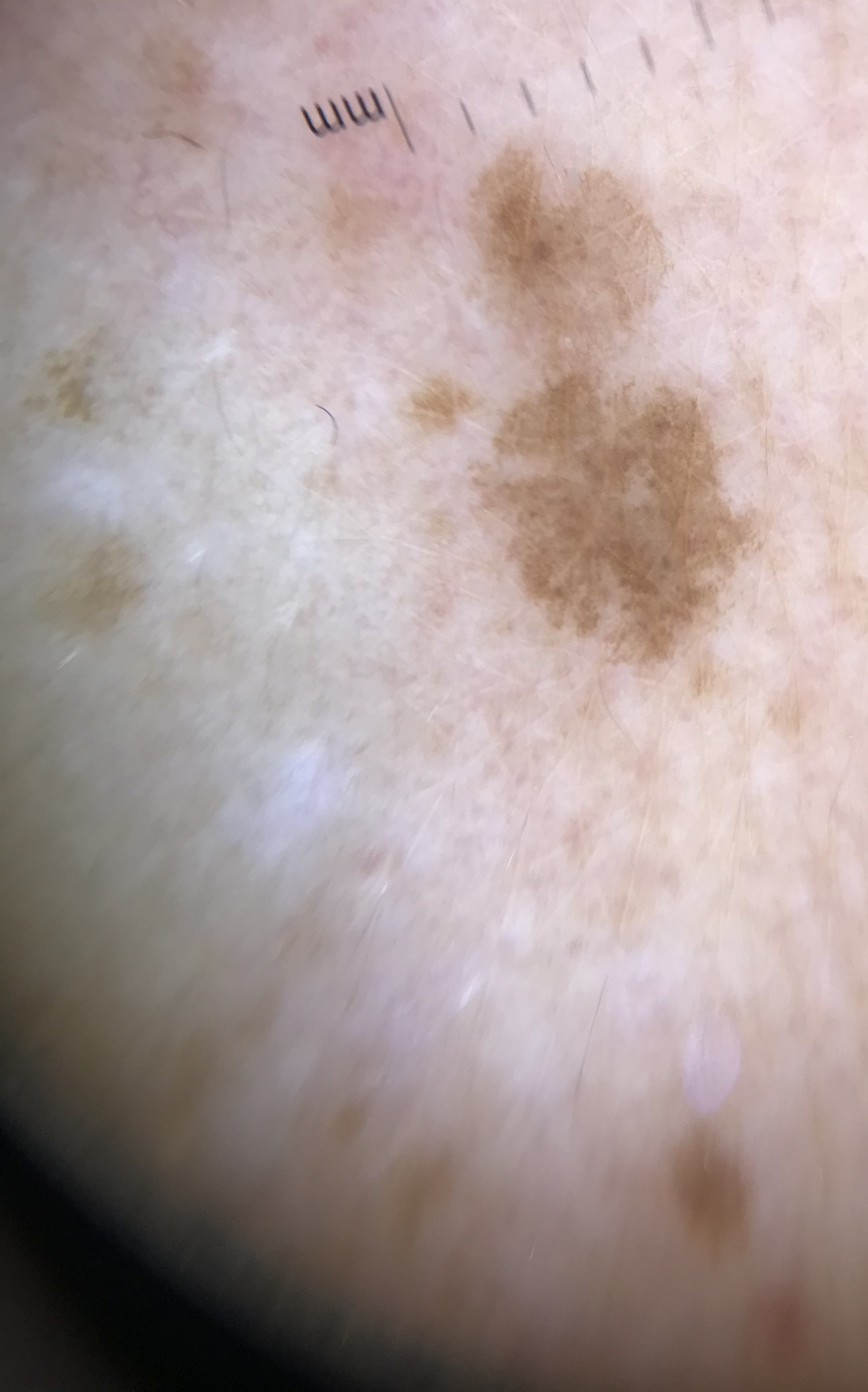A dermoscopic image of a skin lesion. Classified as a benign lesion — a solar lentigo.